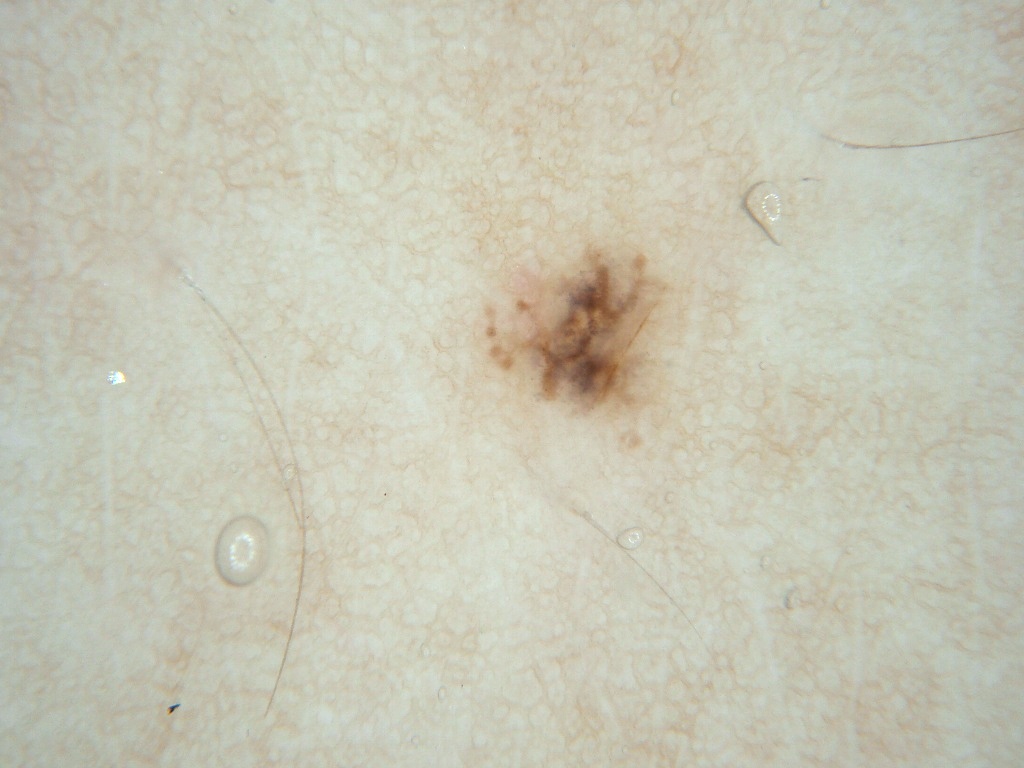A dermoscopic close-up of a skin lesion. The subject is a female in their mid- to late 20s. The lesion spans left=480, top=233, right=682, bottom=425. The dermoscopic pattern shows streaks and globules. Diagnosed as a melanocytic nevus.